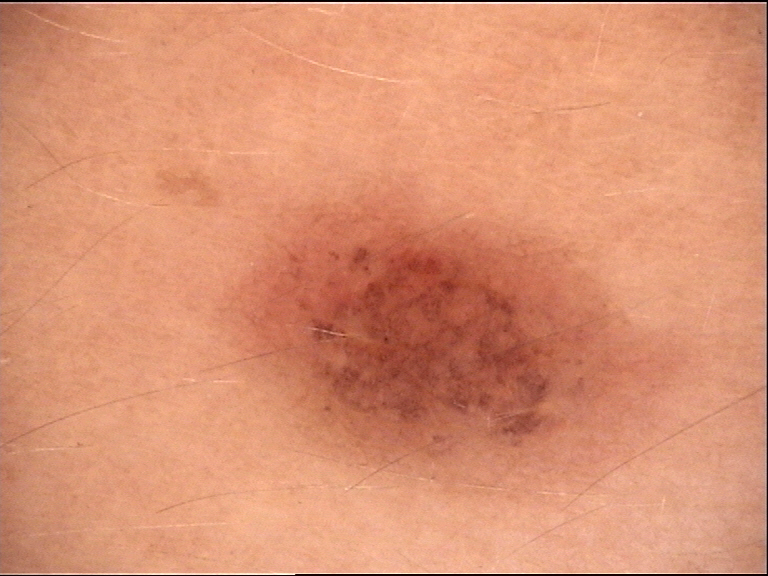label: compound nevus (expert consensus).